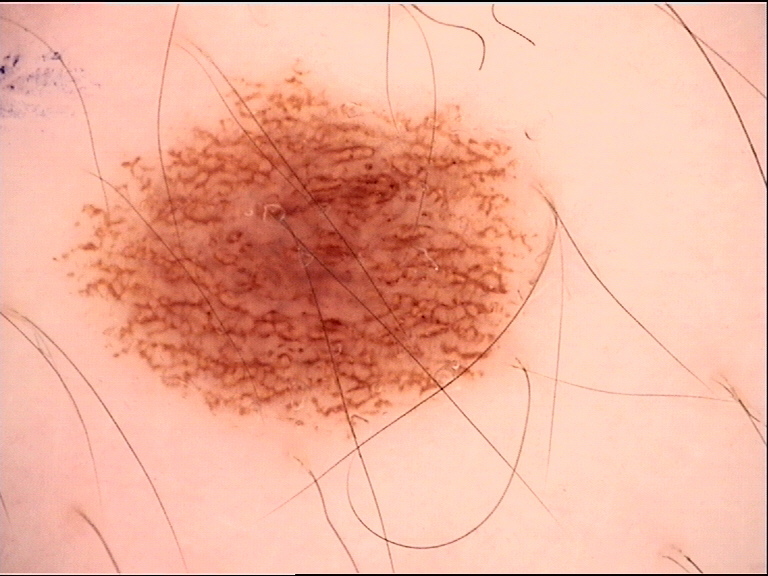Impression: The diagnostic label was a benign lesion — a dysplastic junctional nevus.